Close-up view.
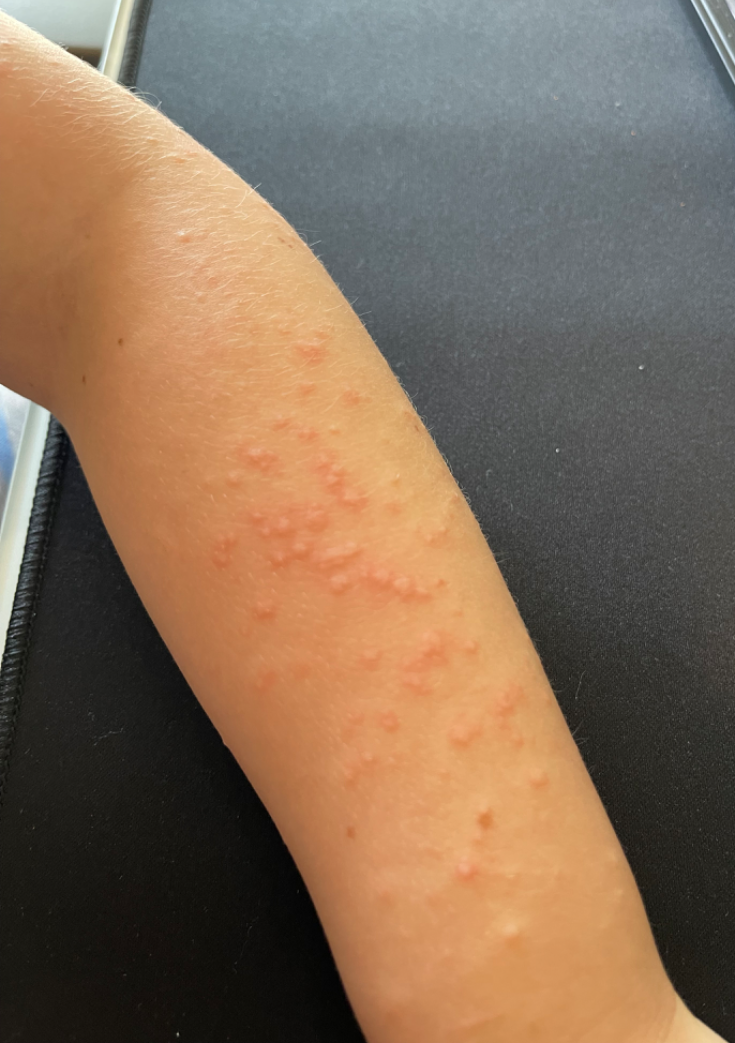Impression: Most consistent with Urticaria; an alternative is Viral Exanthem.